A skin lesion imaged with a dermatoscope.
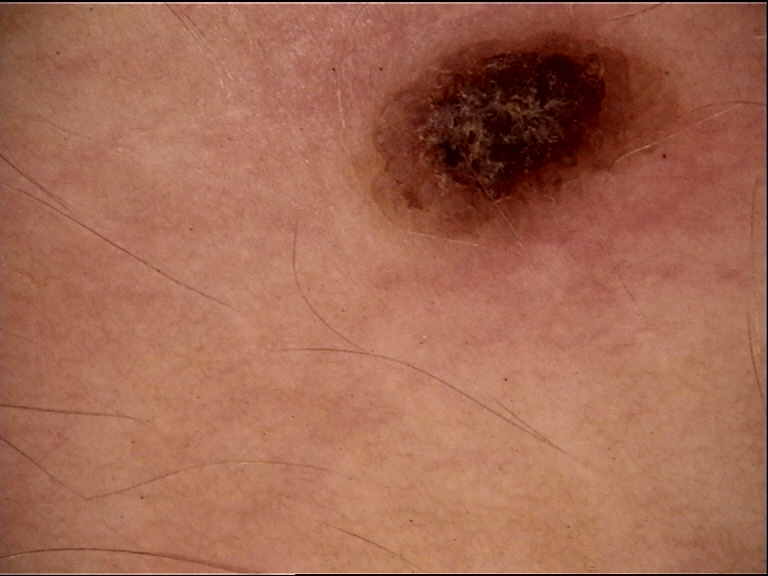The architecture is that of a banal lesion.
The diagnosis was a compound nevus.